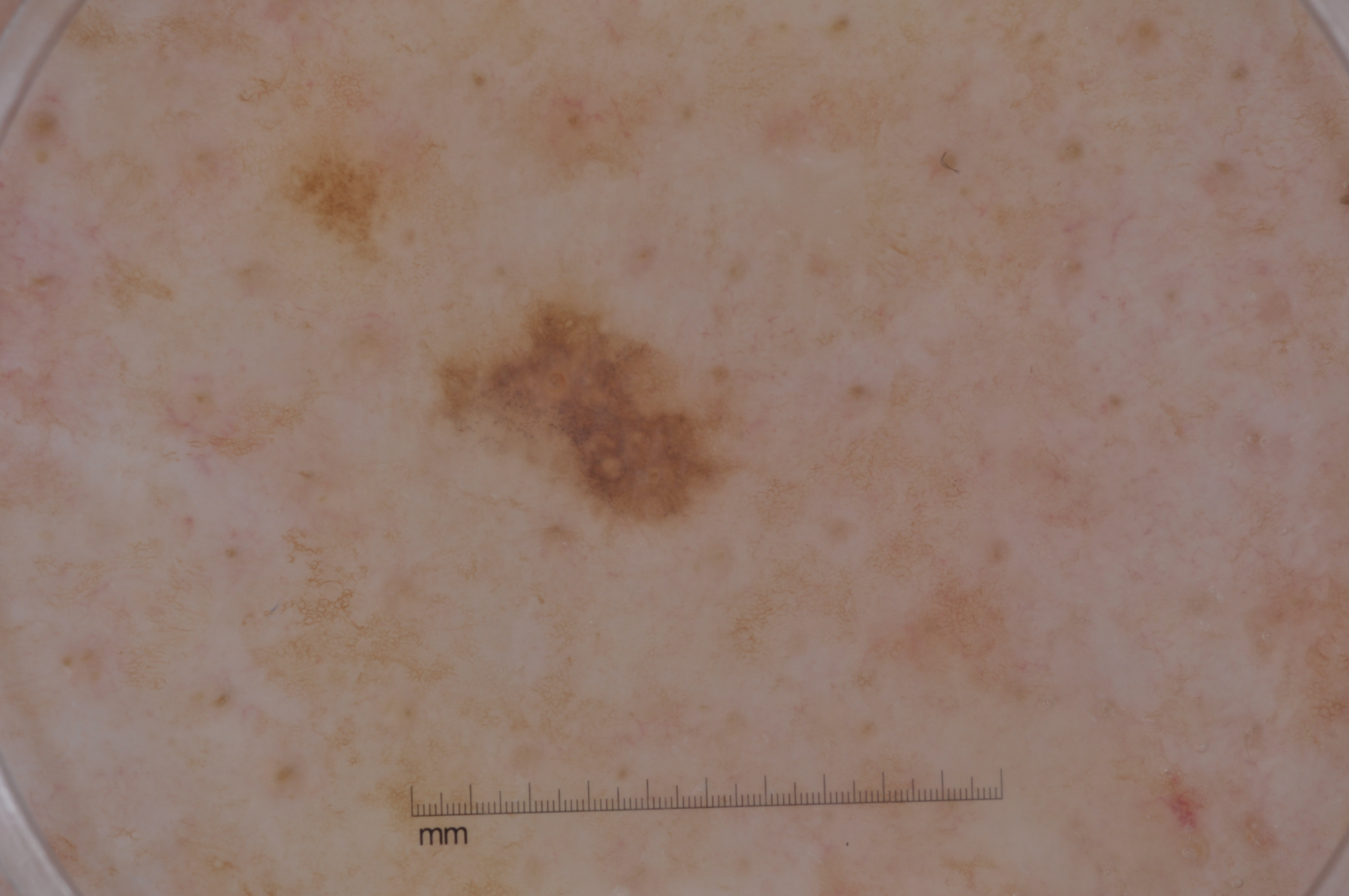Case summary:
- image: dermoscopy
- subject: male, aged approximately 75
- dermoscopic pattern: pigment network
- lesion location: x1=443 y1=294 x2=738 y2=518
- diagnostic label: a melanoma